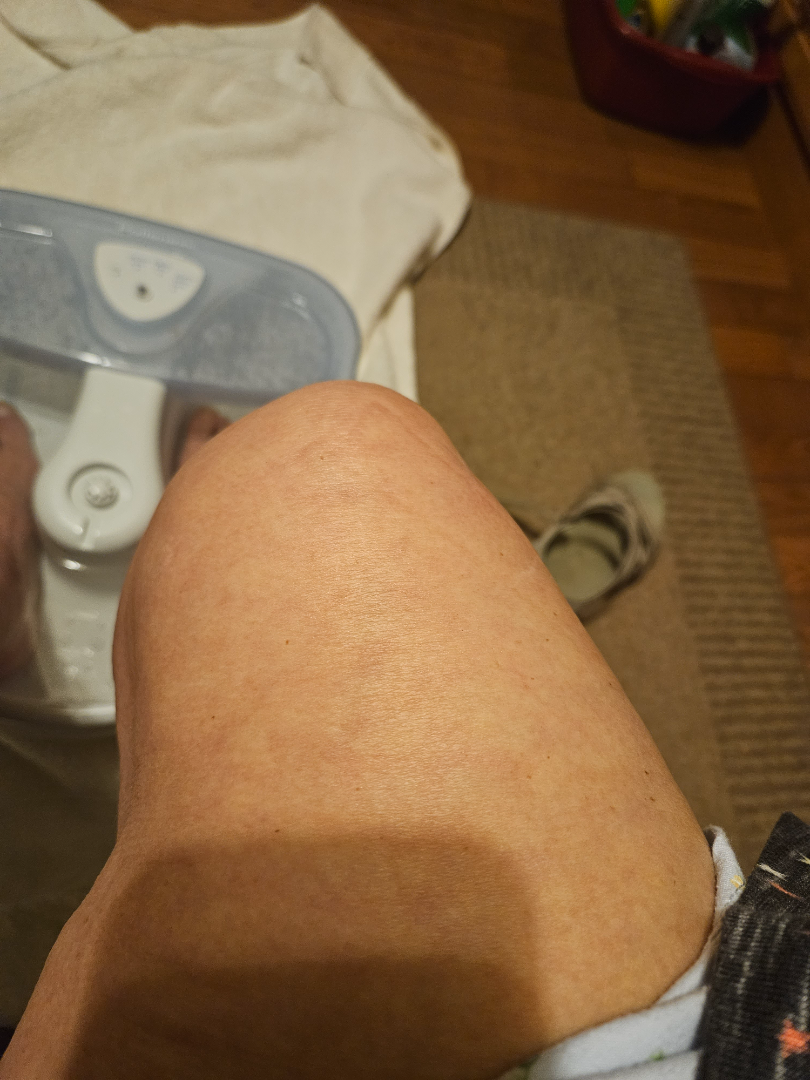Q: Could the case be diagnosed?
A: no discernible pathology
Q: Who is the patient?
A: female, age 70–79
Q: How was the photo taken?
A: close-up
Q: What is the affected area?
A: leg